Imaged for a research study, with no referral diagnosis recorded; a female patient 48 years old; the patient describes having few moles overall; dermoscopy of a skin lesion; the patient reports a family history of skin cancer, a history of sunbed use, no immunosuppression, and no personal history of skin cancer — 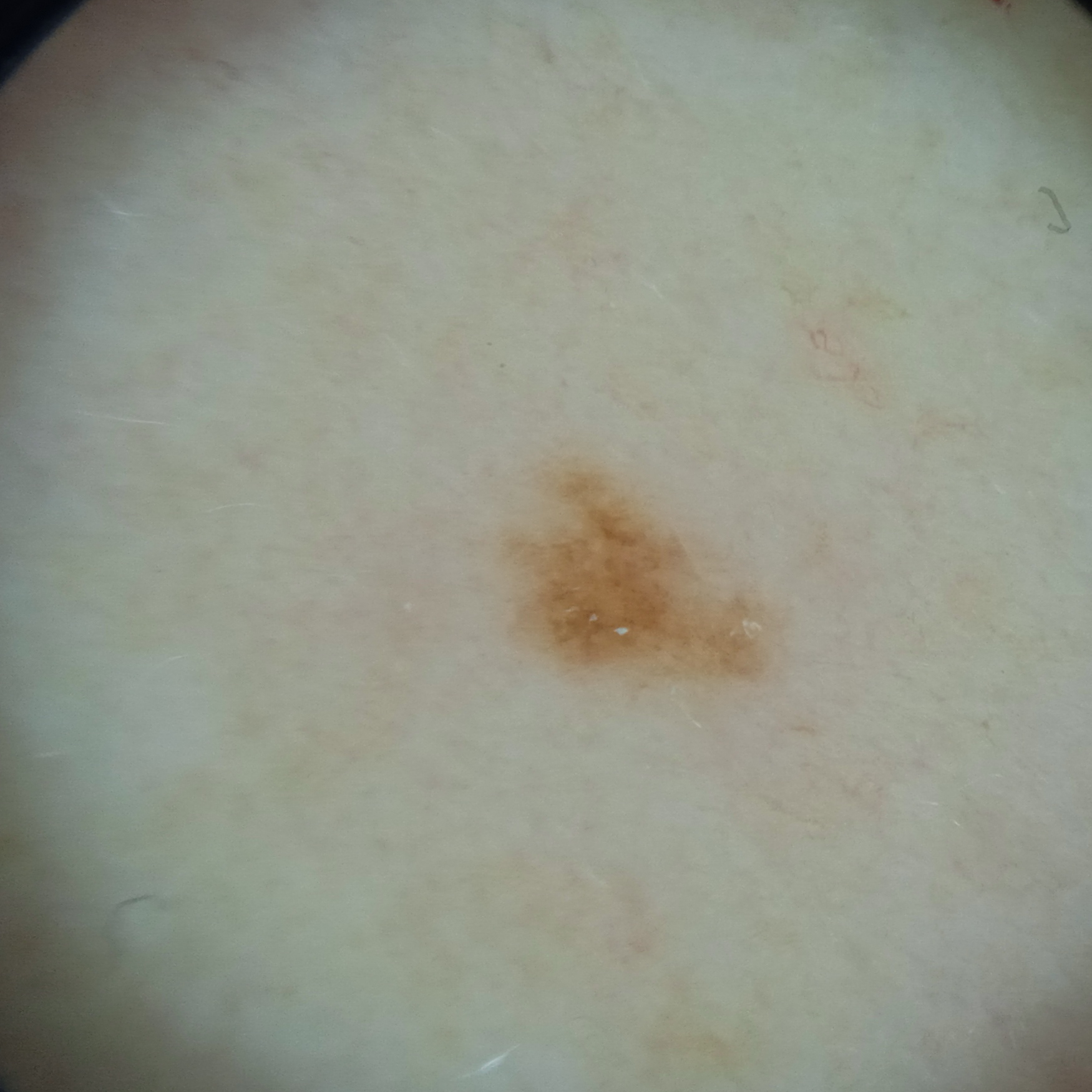The lesion is located on the back. The lesion is about 3.7 mm across. Four dermatologists reviewed the lesion; the consensus was a melanocytic nevus; there was some disagreement among the reviewers.